A wide-field clinical photograph of a skin lesion — 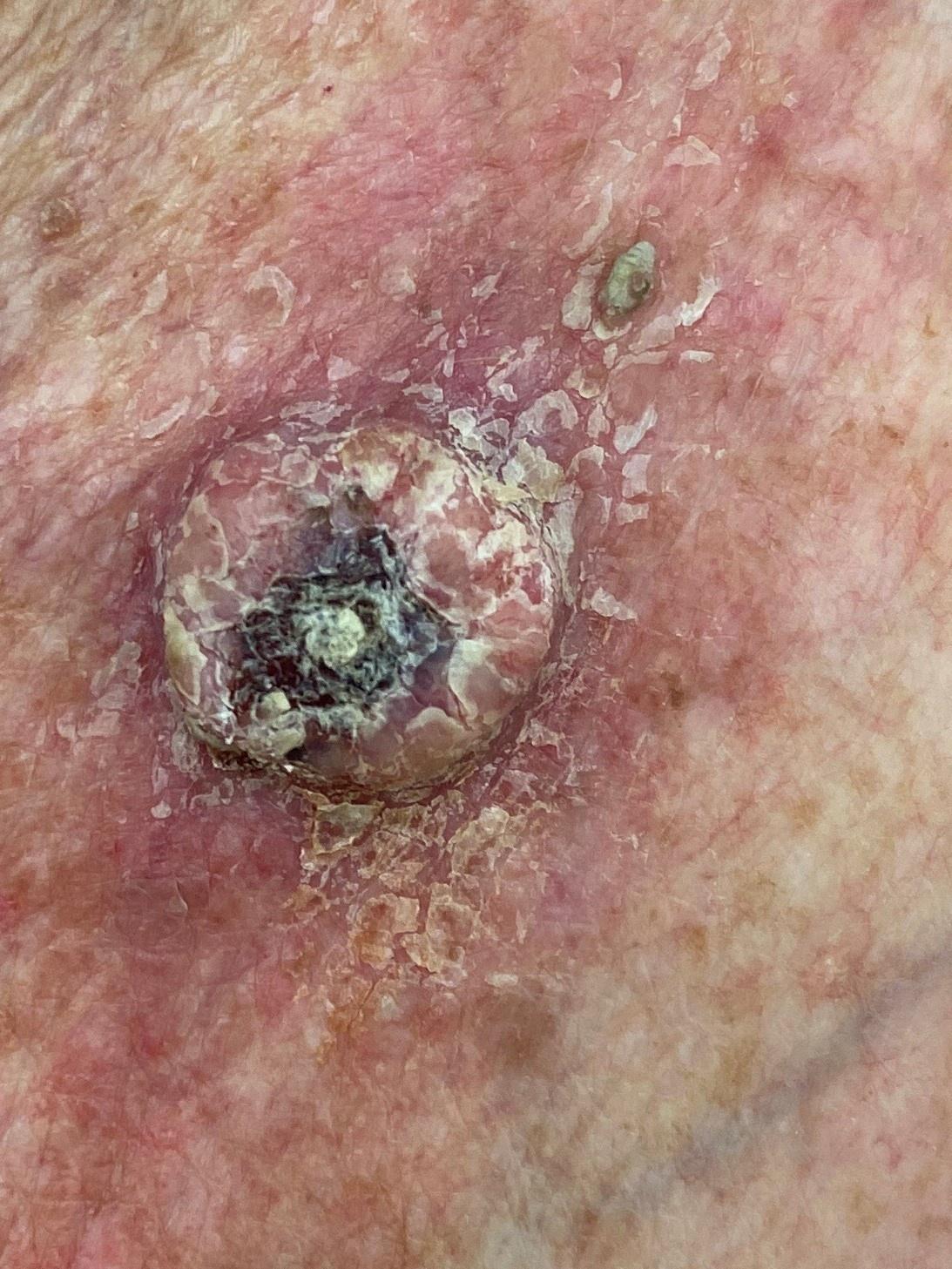Located on the trunk, specifically the anterior trunk.
On biopsy, the diagnosis was a squamous cell carcinoma.